The patient was assessed as skin type II. A clinical close-up photograph of a skin lesion. A female subject 90 years old. By history, prior malignancy (patient or family) and prior skin cancer (patient or family):
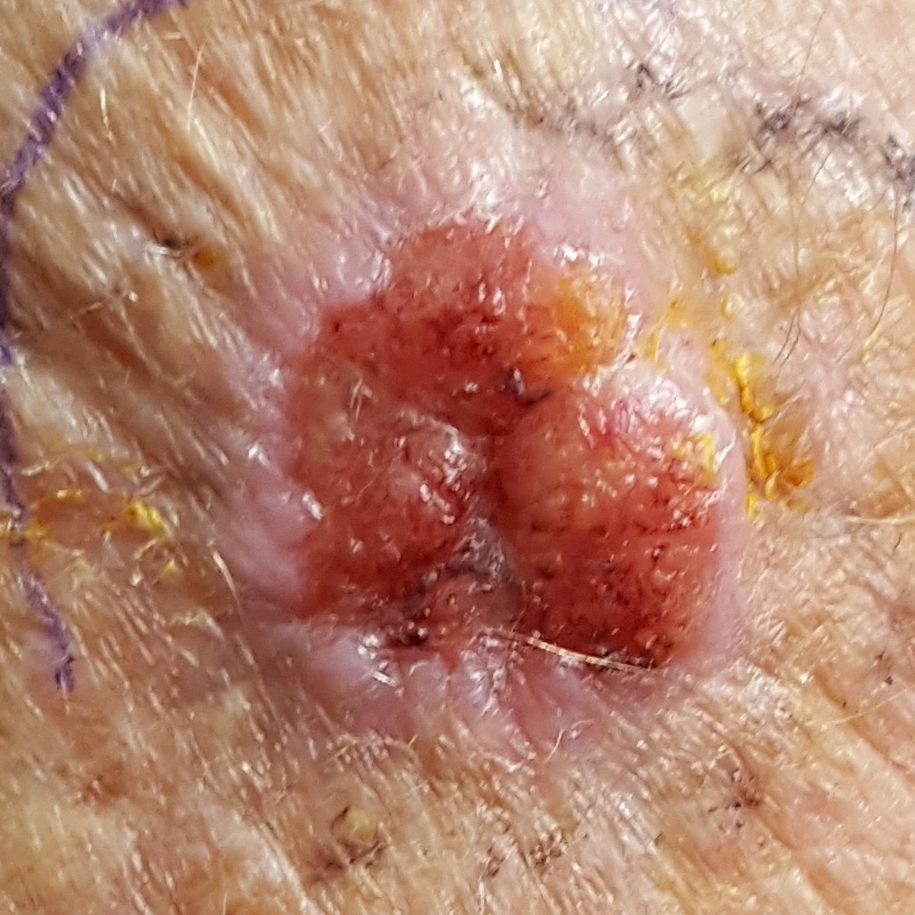The lesion was found on a forearm.
The patient describes that the lesion hurts, has bled, itches, is elevated, and has grown.
Histopathologically confirmed as a malignant skin lesion — a squamous cell carcinoma.